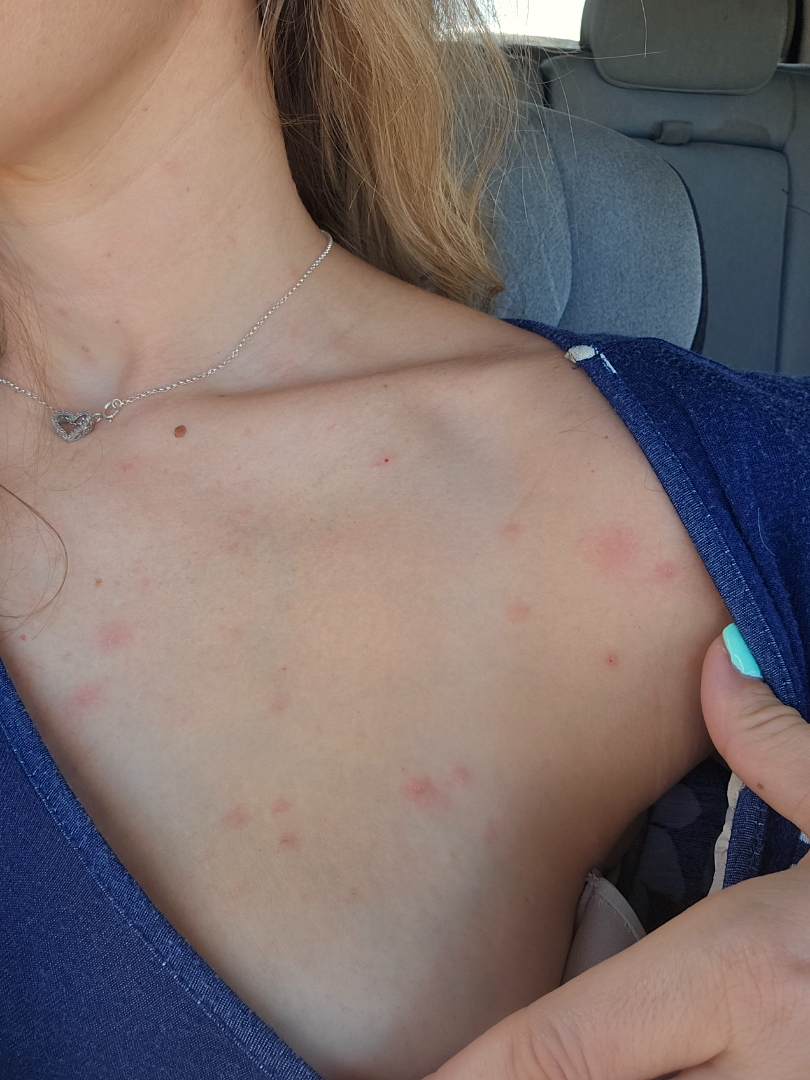The photograph was taken at a distance.
No relevant systemic symptoms.
The patient considered this a rash.
The lesion is associated with itching.
Located on the head or neck, arm, front of the torso and back of the torso.
Reported duration is less than one week.
Female contributor, age 30–39.
The patient notes the lesion is raised or bumpy.
Favoring Insect Bite; also consider Eczema; the differential also includes Urticaria.